The photo was captured at an angle. The affected area is the back of the hand. The patient is 40–49, male: 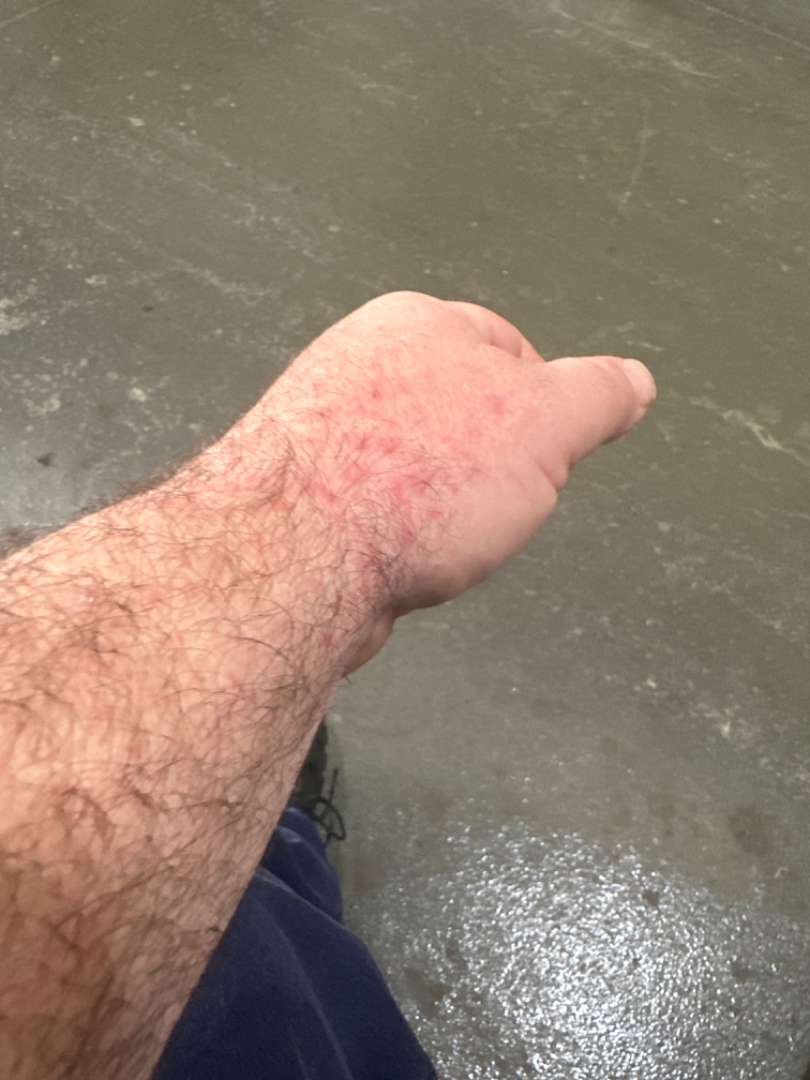Q: Any systemic symptoms?
A: none reported
Q: What is the lesion texture?
A: raised or bumpy
Q: What symptoms does the patient report?
A: itching
Q: Patient's own categorization?
A: a rash
Q: What is the differential diagnosis?
A: the differential is split between Folliculitis, Eczema and Allergic Contact Dermatitis